The photo was captured at a distance · symptoms reported: enlargement, itching and burning · no relevant systemic symptoms · the contributor is a female aged 30–39 · present for about one day · the leg, back of the hand, head or neck and arm are involved:
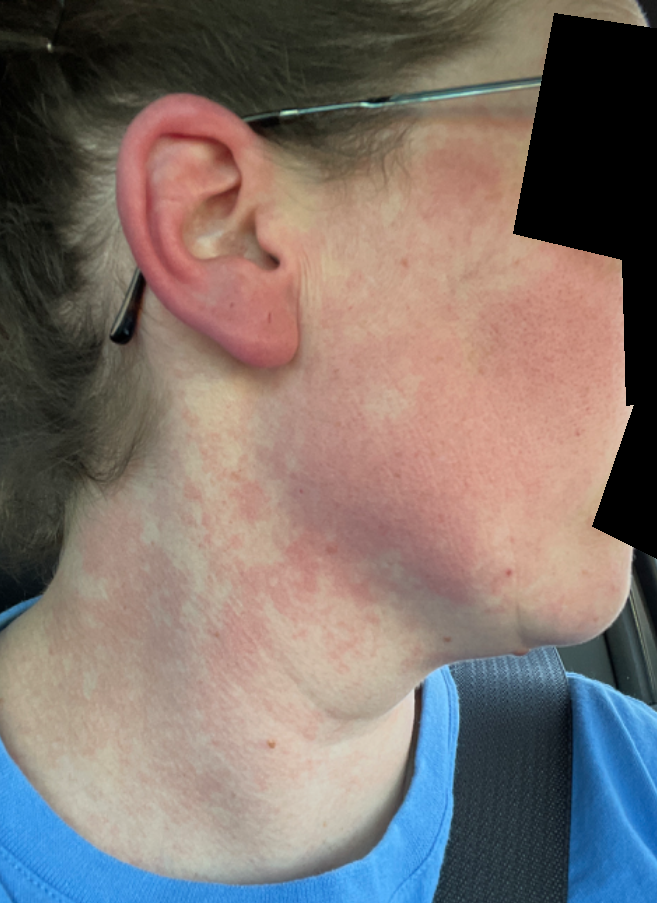impression: Allergic Contact Dermatitis (most likely); Rosacea (possible); Irritant Contact Dermatitis (remote).